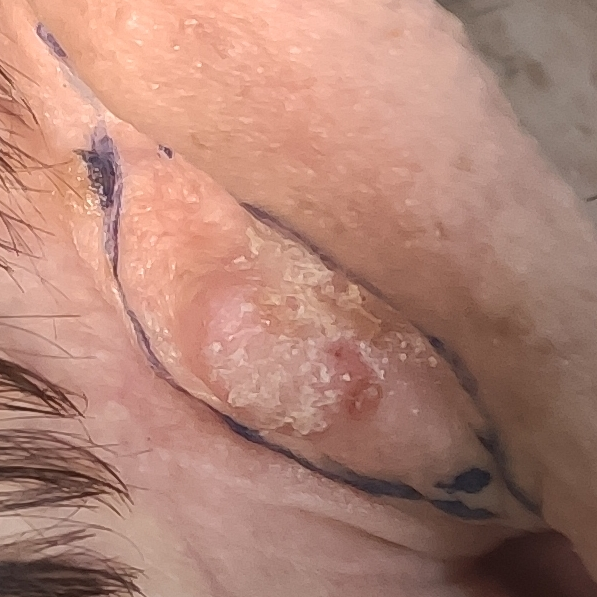risk factors=pesticide exposure, tobacco use, prior skin cancer (patient or family), prior malignancy (patient or family) | FST=III | reported symptoms=change in appearance, elevation, growth, itching / no bleeding | pathology=squamous cell carcinoma (biopsy-proven).